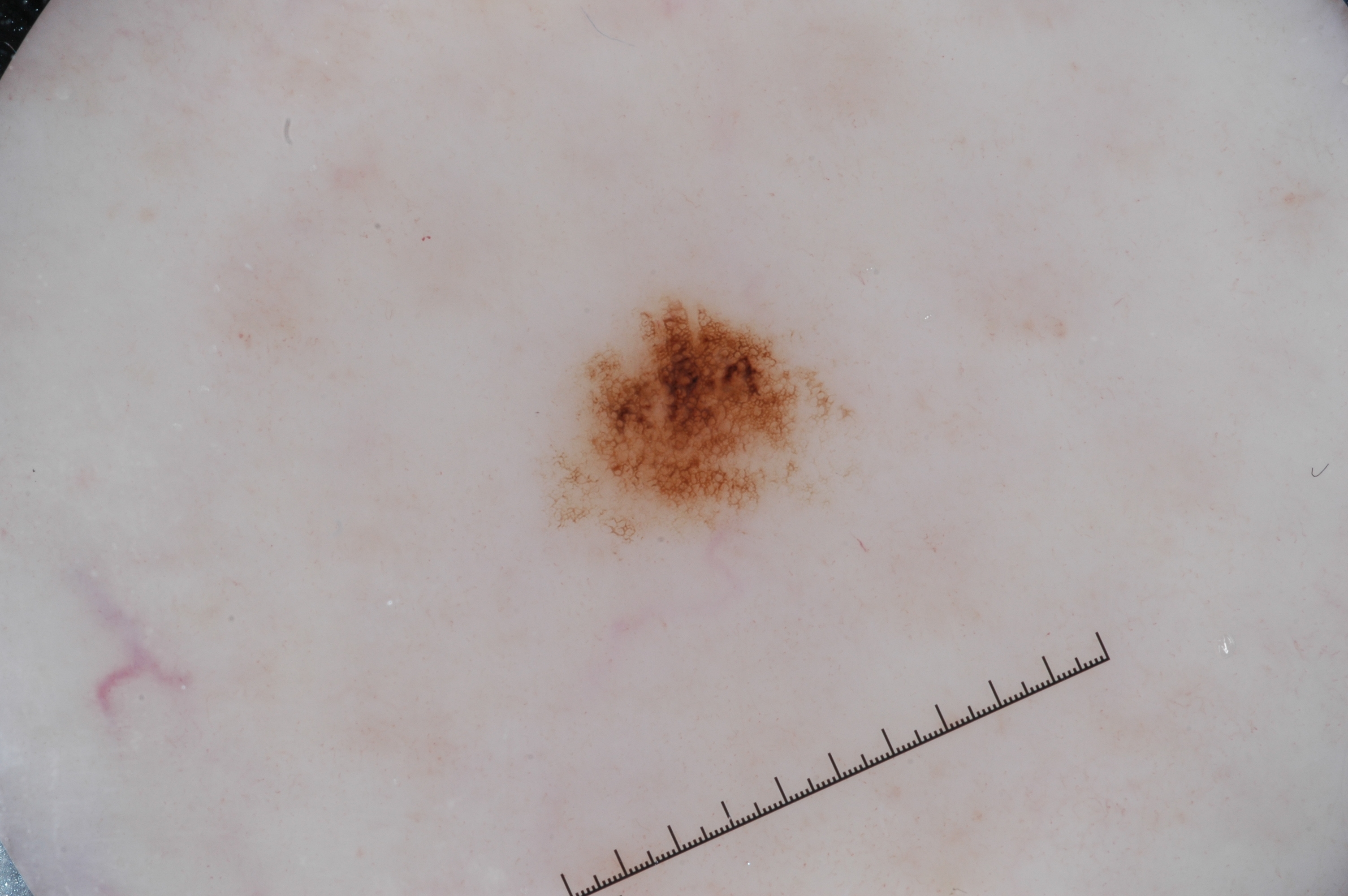Dermoscopy of a skin lesion.
A female subject, aged 58-62.
The lesion is bounded by x1=558, y1=294, x2=832, y2=539.
The dermoscopic pattern shows pigment network.
A small lesion occupying a minor part of the field.
Expert review diagnosed this as a melanocytic nevus.